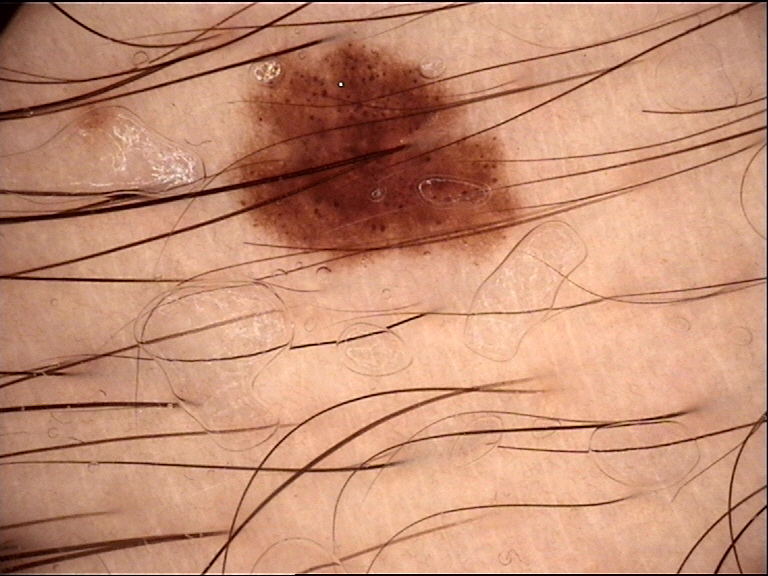A dermoscopy image of a single skin lesion. The diagnostic label was a benign lesion — a dysplastic junctional nevus.